Reported duration is less than one week. Located on the back of the torso. The patient also reports joint pain. Close-up view. Texture is reported as raised or bumpy. Reported lesion symptoms include enlargement, itching and pain.
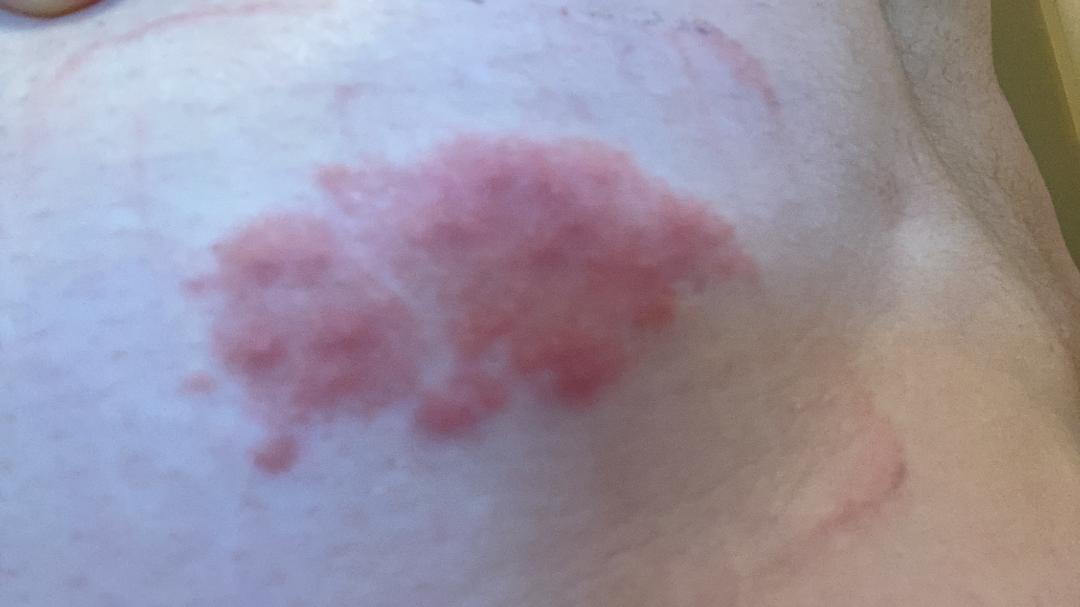Single-reviewer assessment: Impetigo, Eczema and Allergic Contact Dermatitis were each considered, in no particular order.